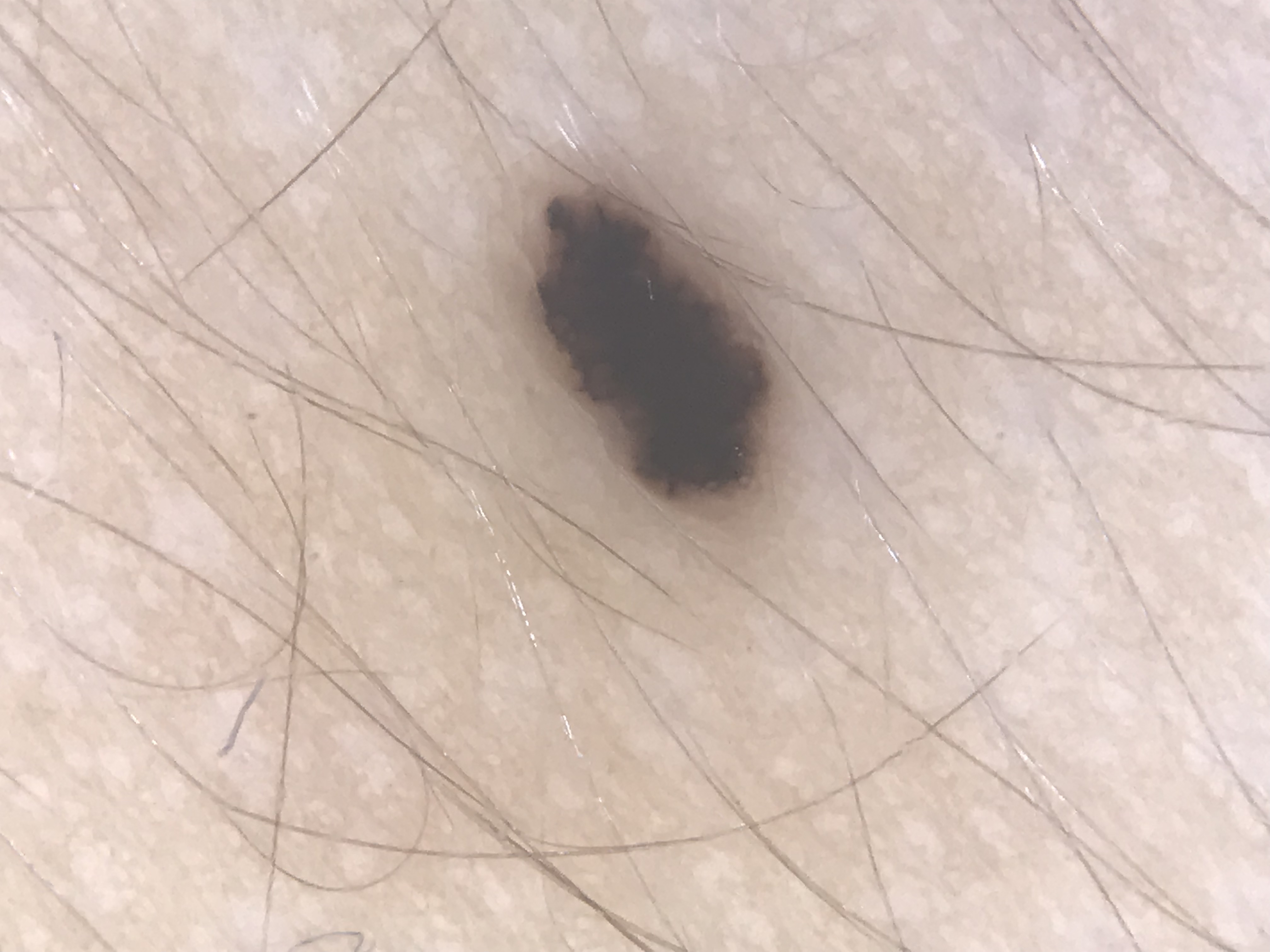A dermoscopic photograph of a skin lesion. The diagnosis was a dysplastic junctional nevus.